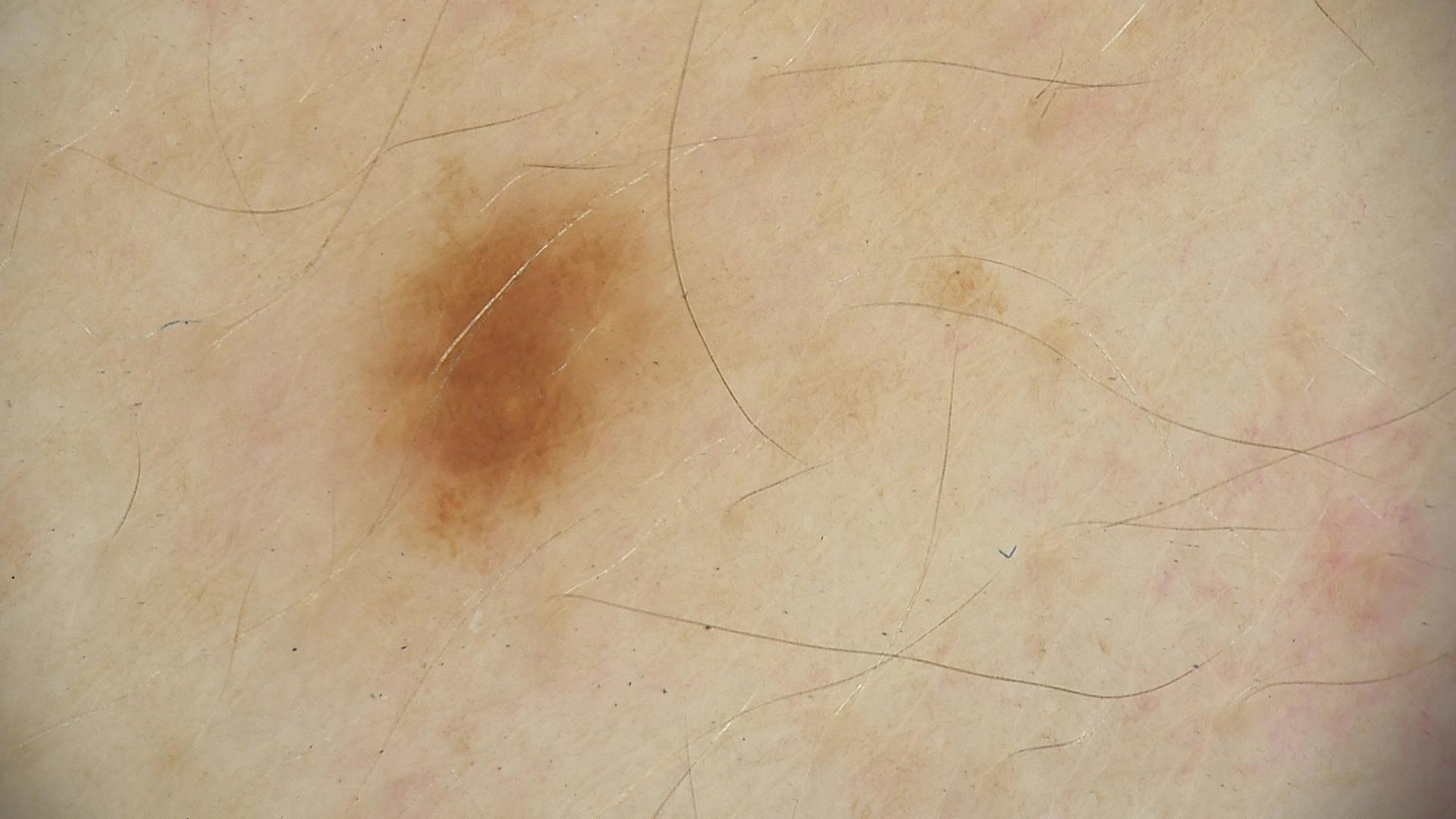diagnosis — junctional nevus (expert consensus).